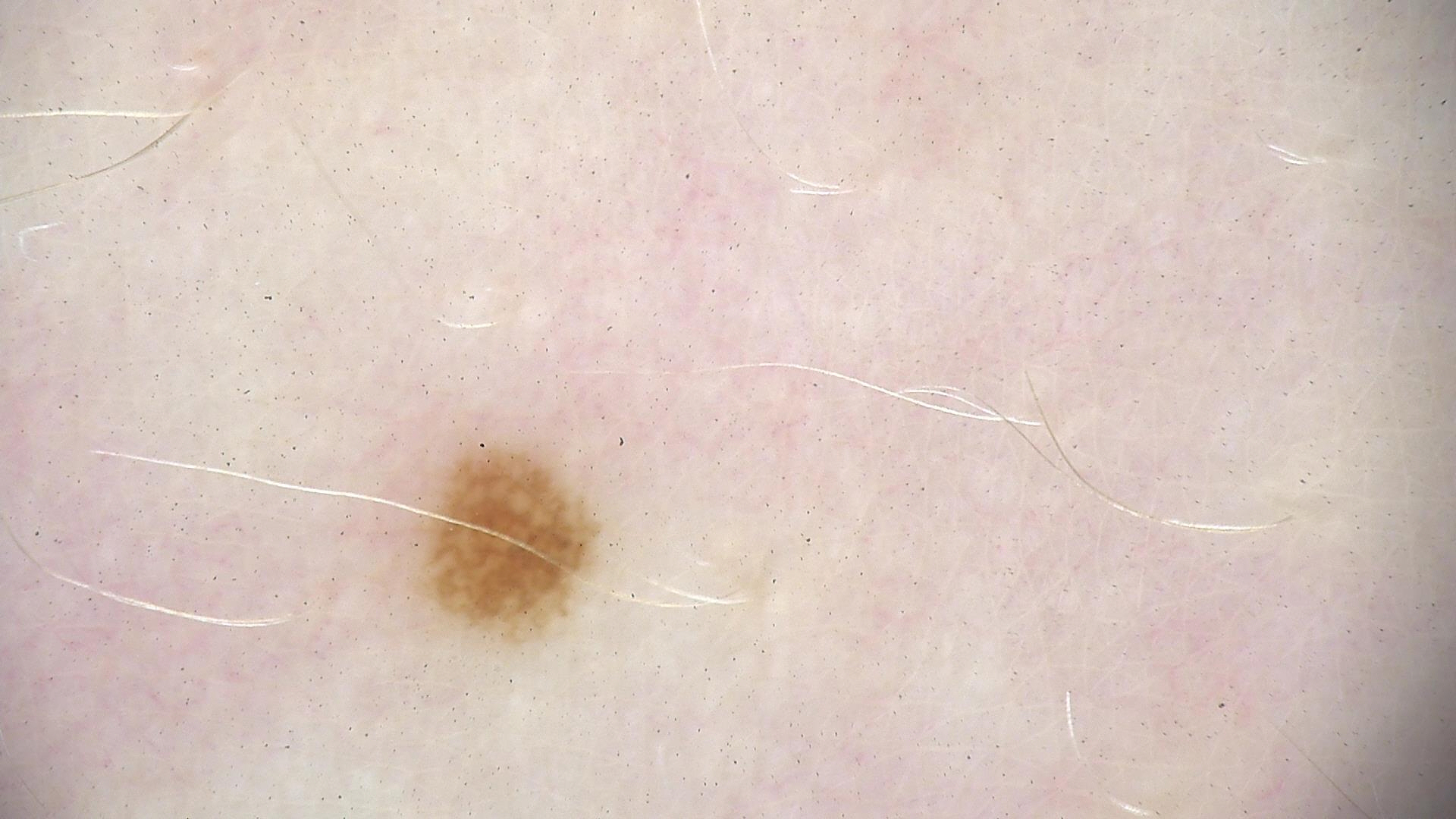The diagnostic label was a dysplastic junctional nevus.